On a questionnaire the patient reported a personal history of skin cancer, a personal history of cancer, no prior organ transplant, and no immunosuppression; the patient says their skin tans without first burning; dermoscopy of a skin lesion; the patient describes having few moles overall: 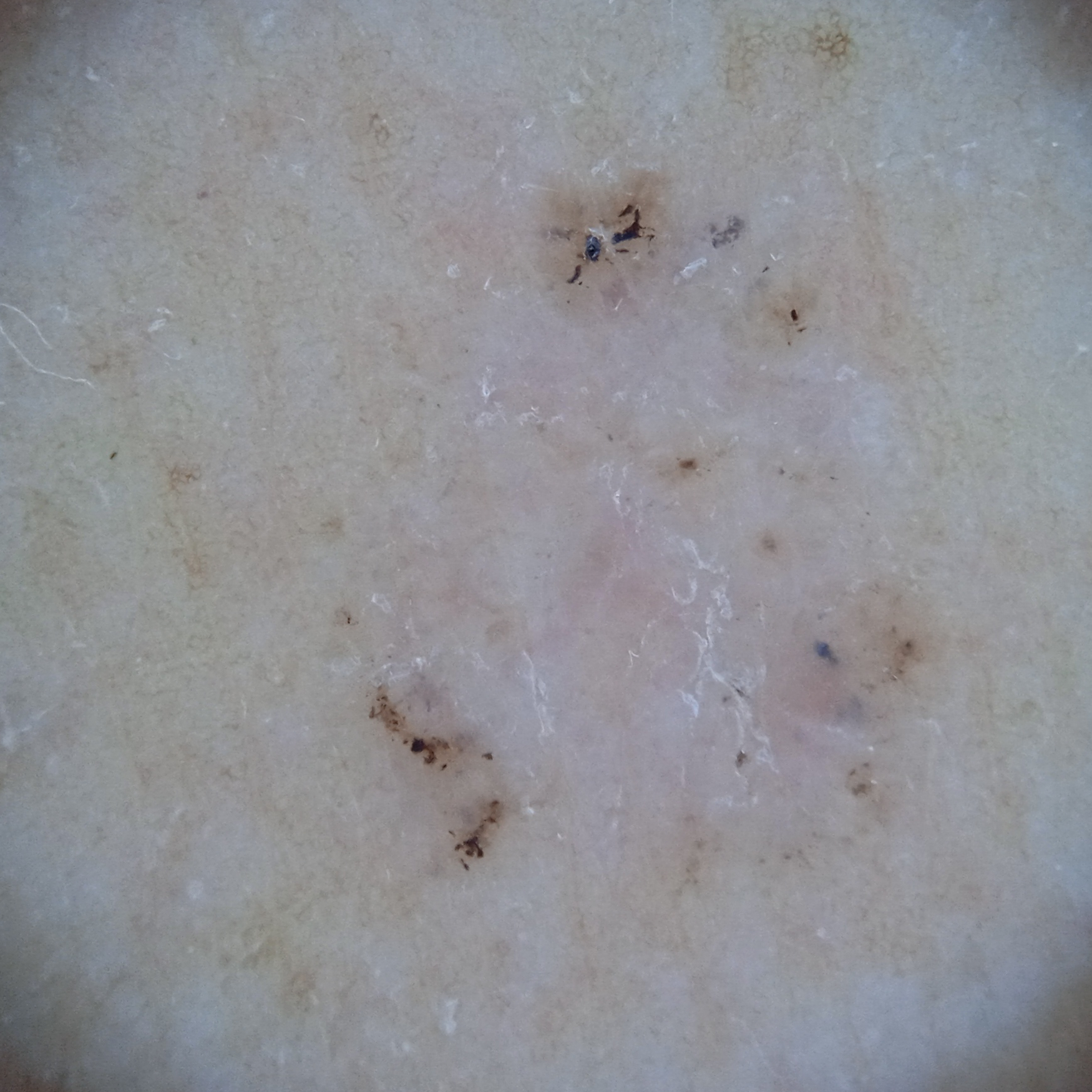Assessment: The four-dermatologist consensus diagnosis was a basal cell carcinoma; all four reviewers agreed; diagnostic confidence was good.